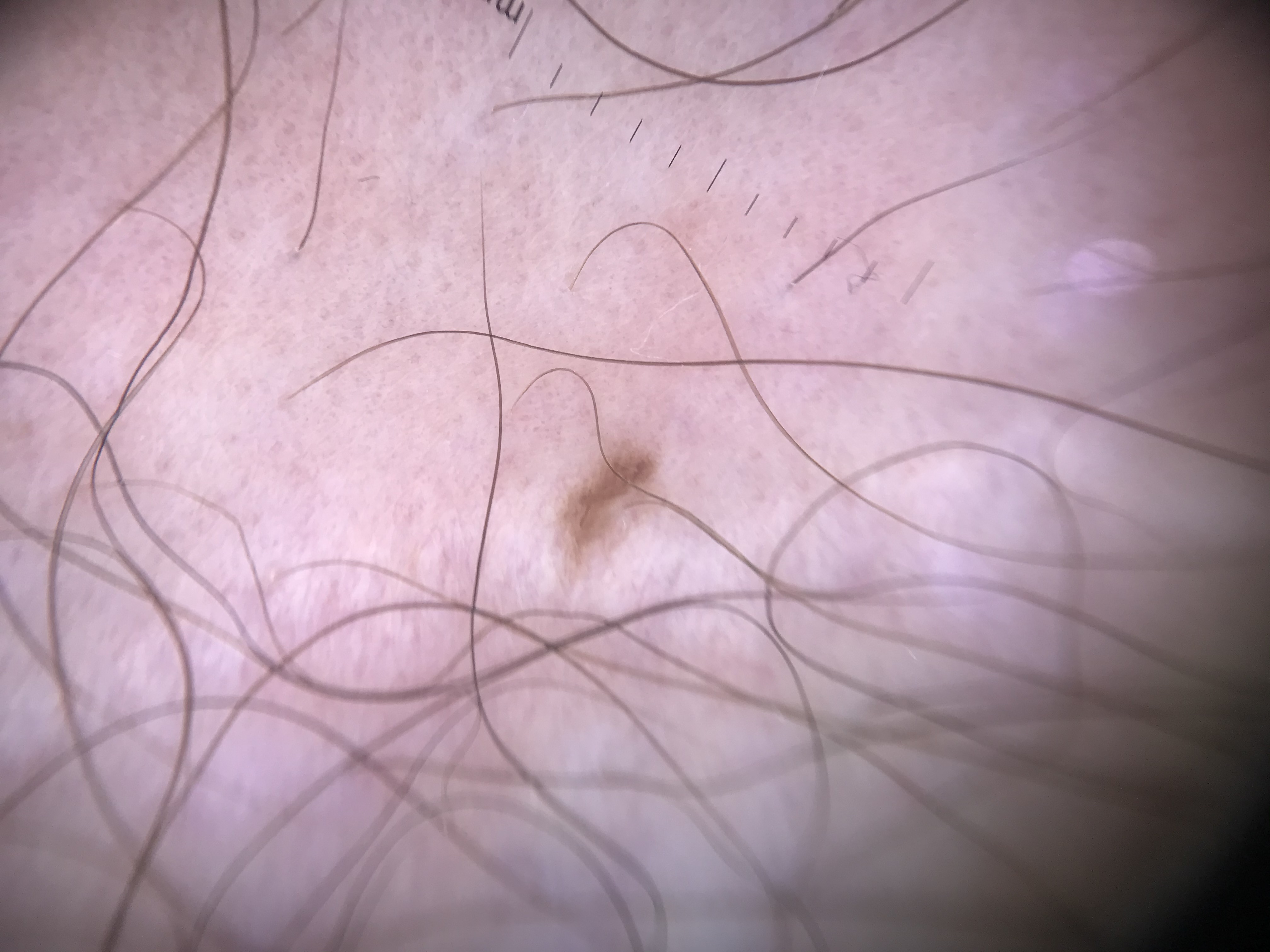diagnosis:
  name: junctional nevus
  code: jb
  malignancy: benign
  super_class: melanocytic
  confirmation: expert consensus